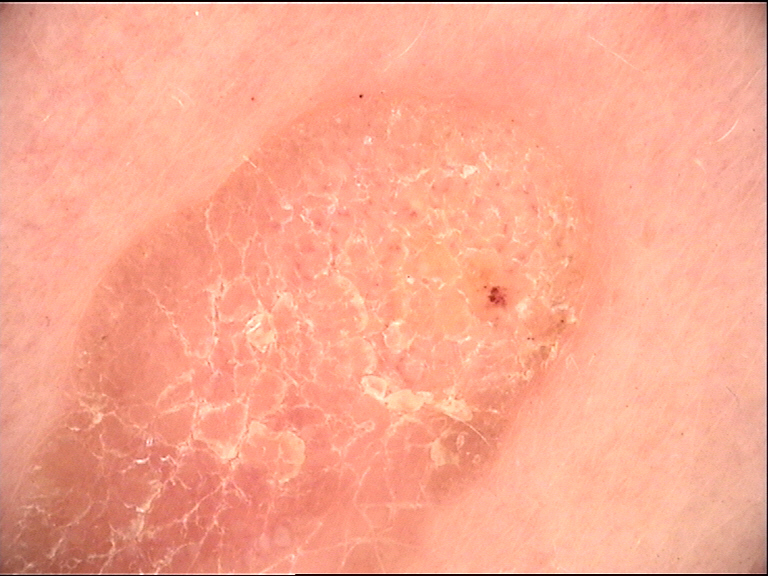{
  "diagnosis": {
    "name": "seborrheic keratosis",
    "code": "sk",
    "malignancy": "benign",
    "super_class": "non-melanocytic",
    "confirmation": "expert consensus"
  }
}